The chart notes a previous melanoma but no melanoma in first-degree relatives; a male patient aged 53 to 57 — 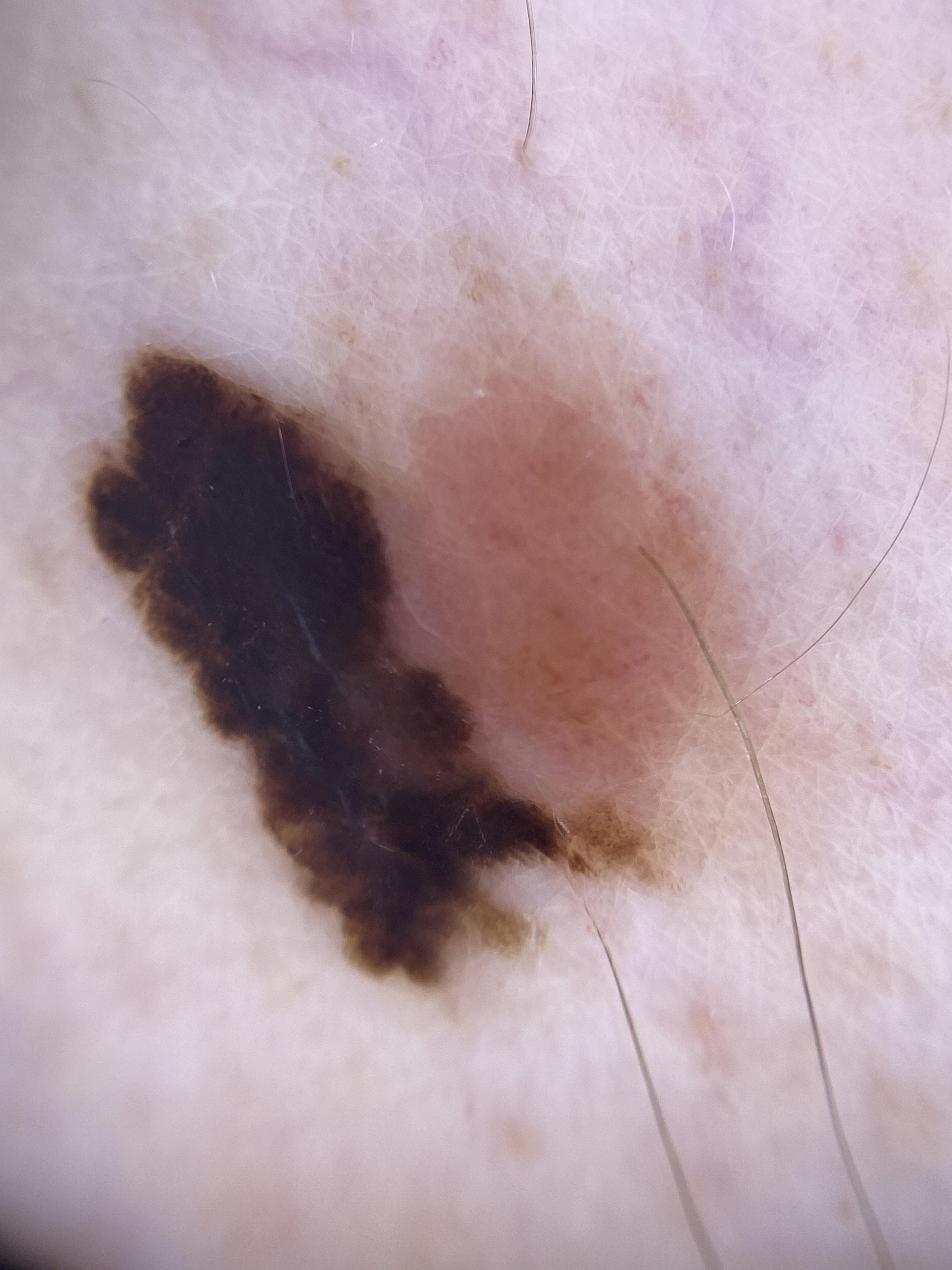Histopathological examination showed a skin cancer — a melanoma.